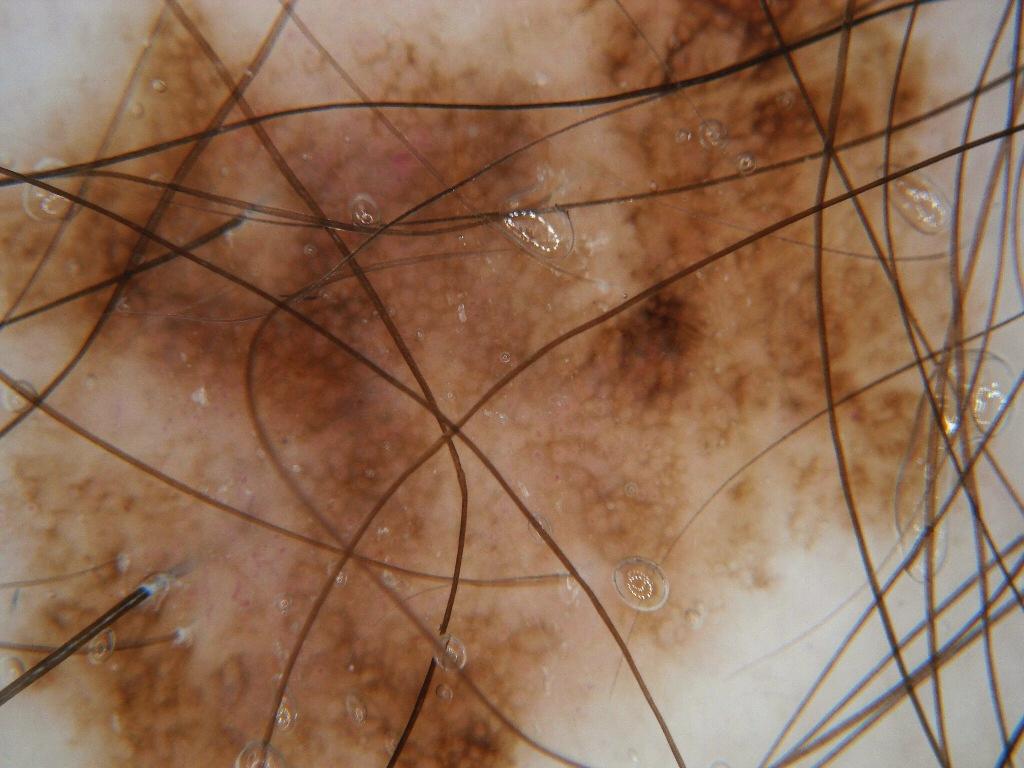A skin lesion imaged with a dermatoscope.
The lesion spans essentially the entire dermoscopic field.
Diagnosed as a benign skin lesion.